A dermoscopy image of a single skin lesion.
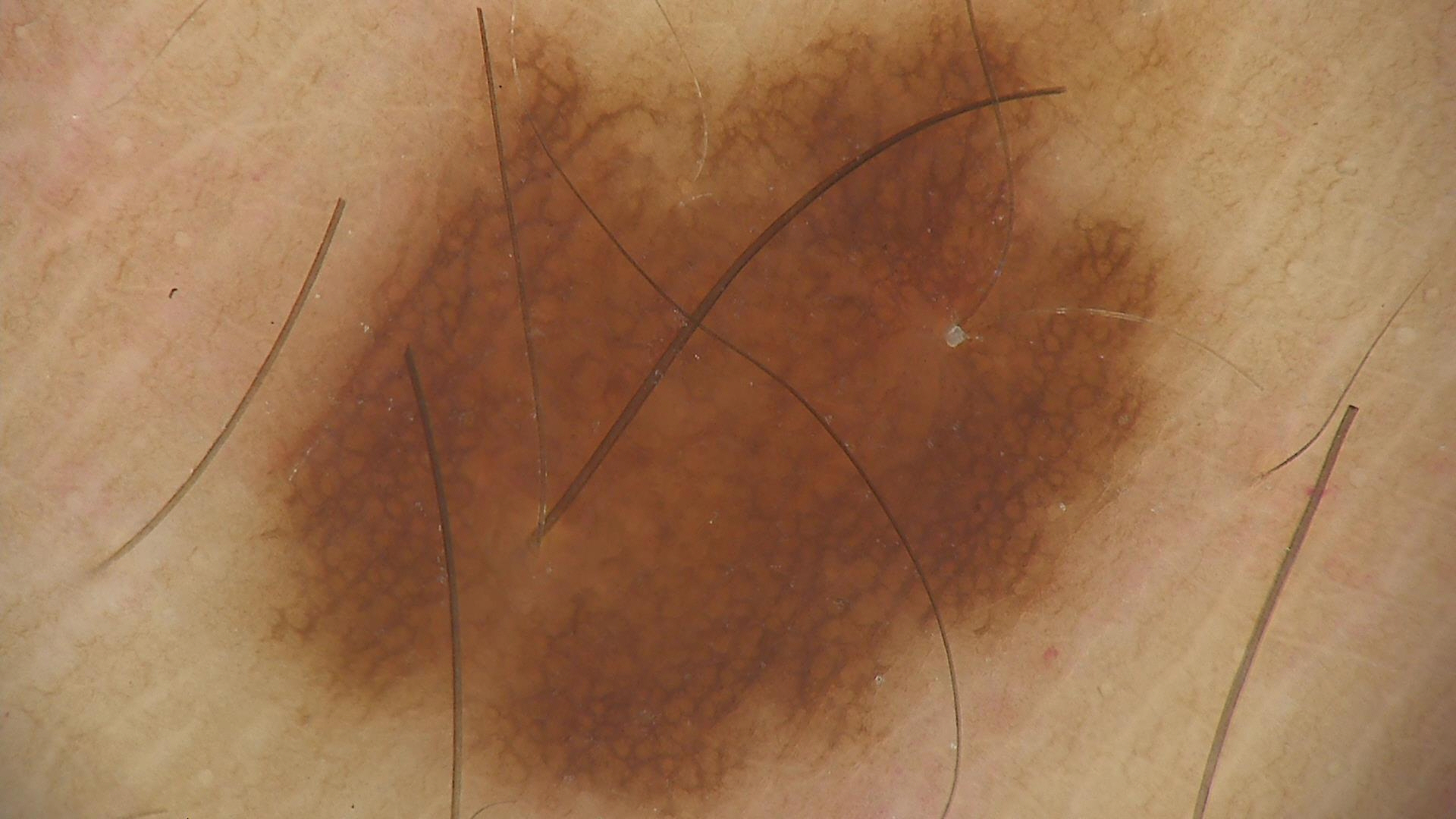<case>
  <diagnosis>
    <name>junctional nevus</name>
    <code>jb</code>
    <malignancy>benign</malignancy>
    <super_class>melanocytic</super_class>
    <confirmation>expert consensus</confirmation>
  </diagnosis>
</case>